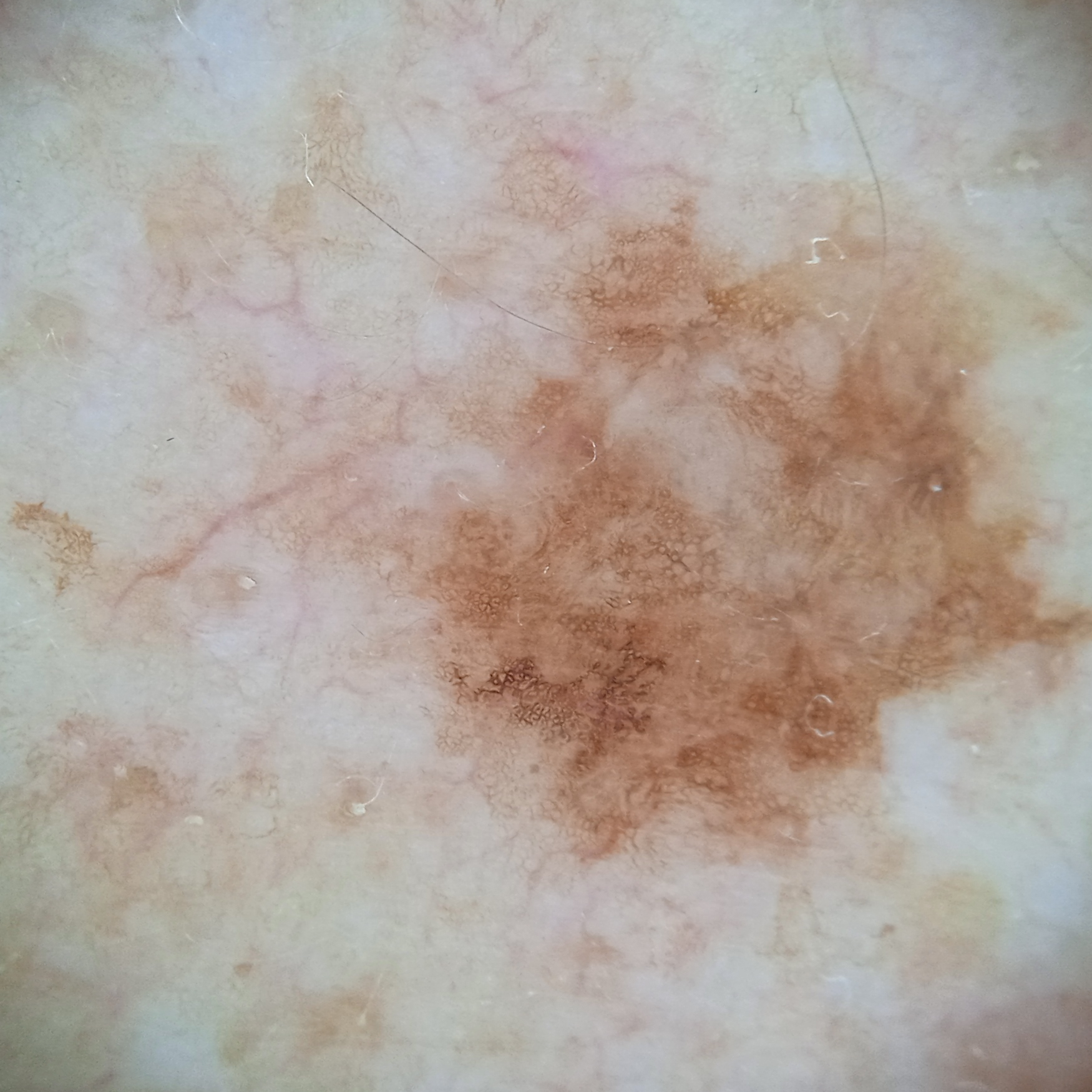The reviewing dermatologists could not reach a confident diagnosis. Summary: The patient describes having few moles overall. Imaged for a research study, with no referral diagnosis recorded. The patient says their skin reddens with sun exposure. The patient reports a personal history of cancer and a family history of skin cancer. The lesion involves the back. The lesion is about 8 mm across.